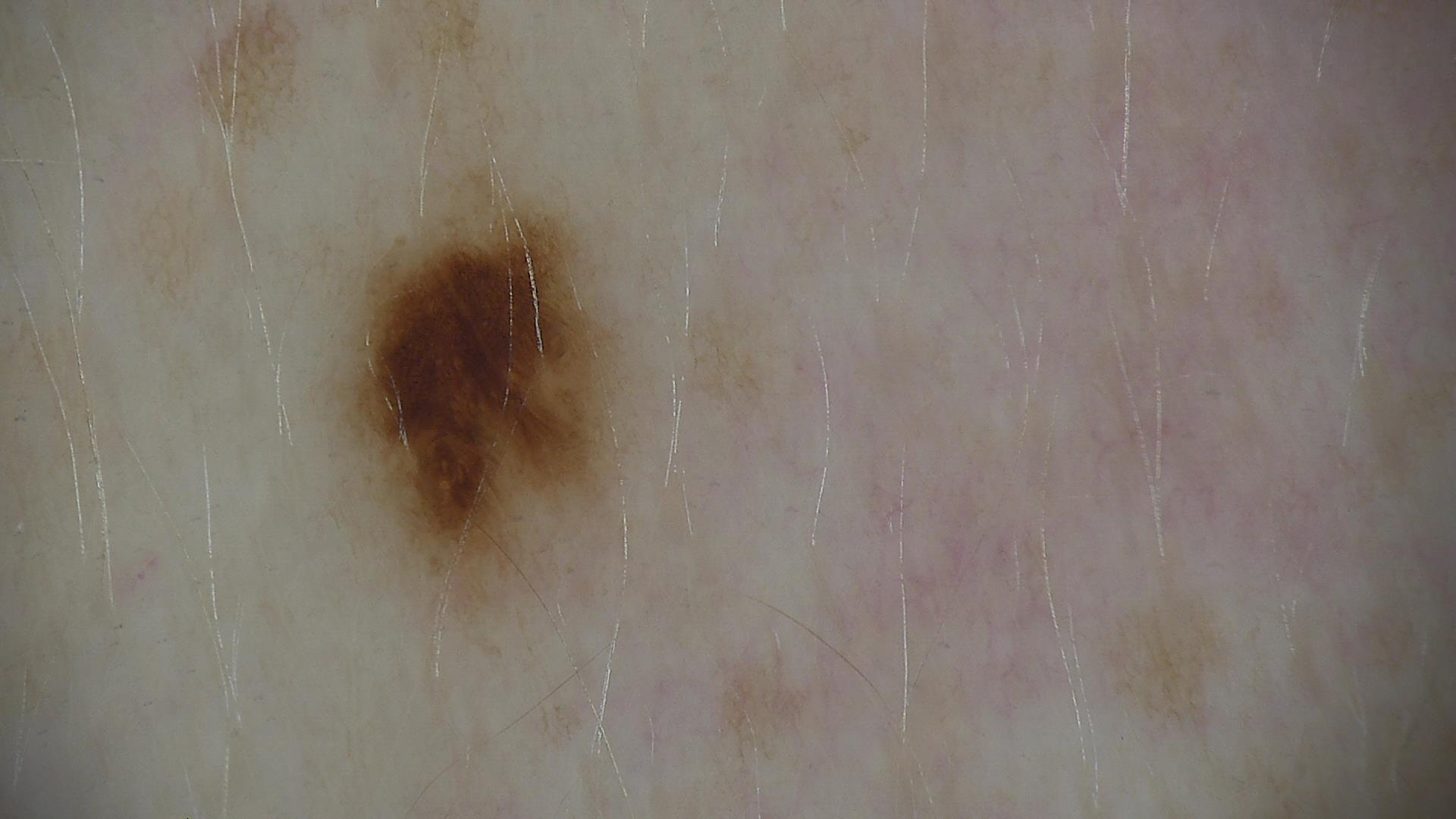{"image": "dermoscopy", "diagnosis": {"name": "dysplastic junctional nevus", "code": "jd", "malignancy": "benign", "super_class": "melanocytic", "confirmation": "expert consensus"}}